A dermatoscopic image of a skin lesion:
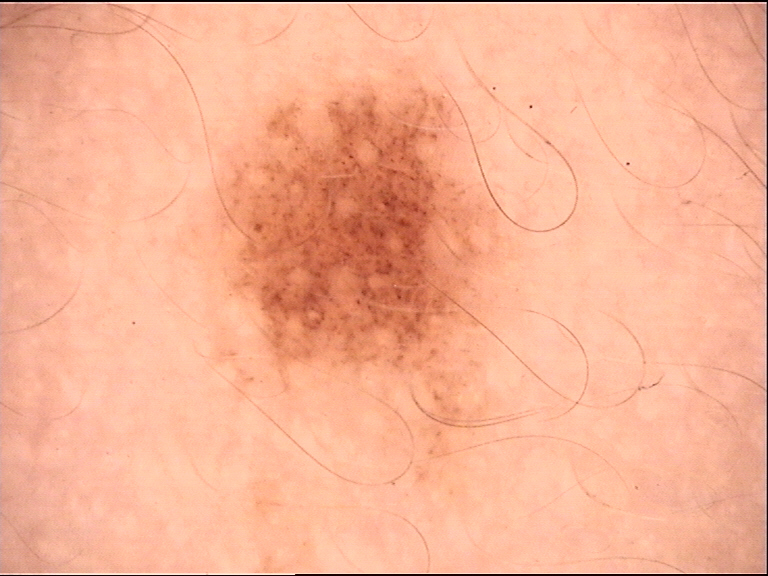Labeled as a dysplastic junctional nevus.